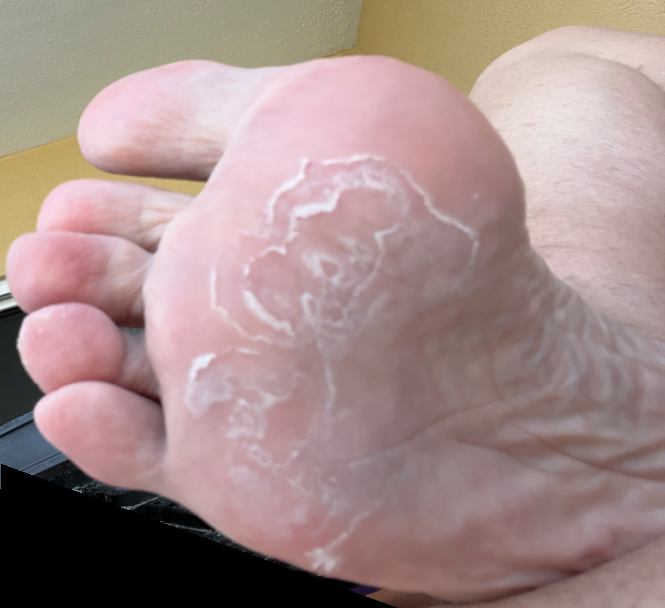The patient is 70–79, female.
This is a close-up image.
Located on the sole of the foot.
On dermatologist assessment of the image: the primary impression is Keratolysis exfoliativa; also raised was Tinea; also consider Eczema.